A dermoscopic close-up of a skin lesion, the subject is a male about 80 years old.
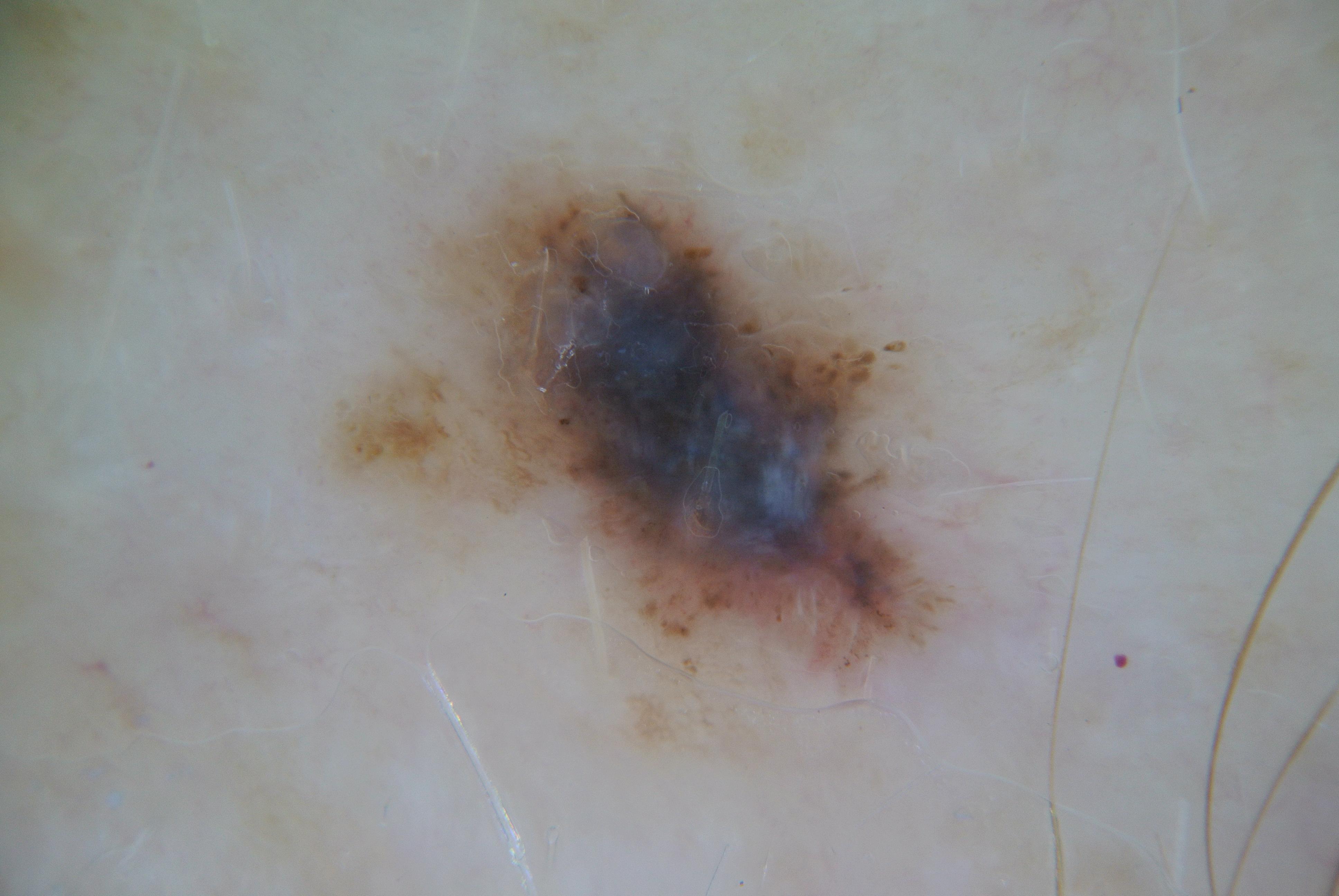Q: What does dermoscopy show?
A: streaks and pigment network
Q: What is the lesion's bounding box?
A: 313, 117, 1021, 758
Q: What is the diagnosis?
A: a melanoma, a malignancy